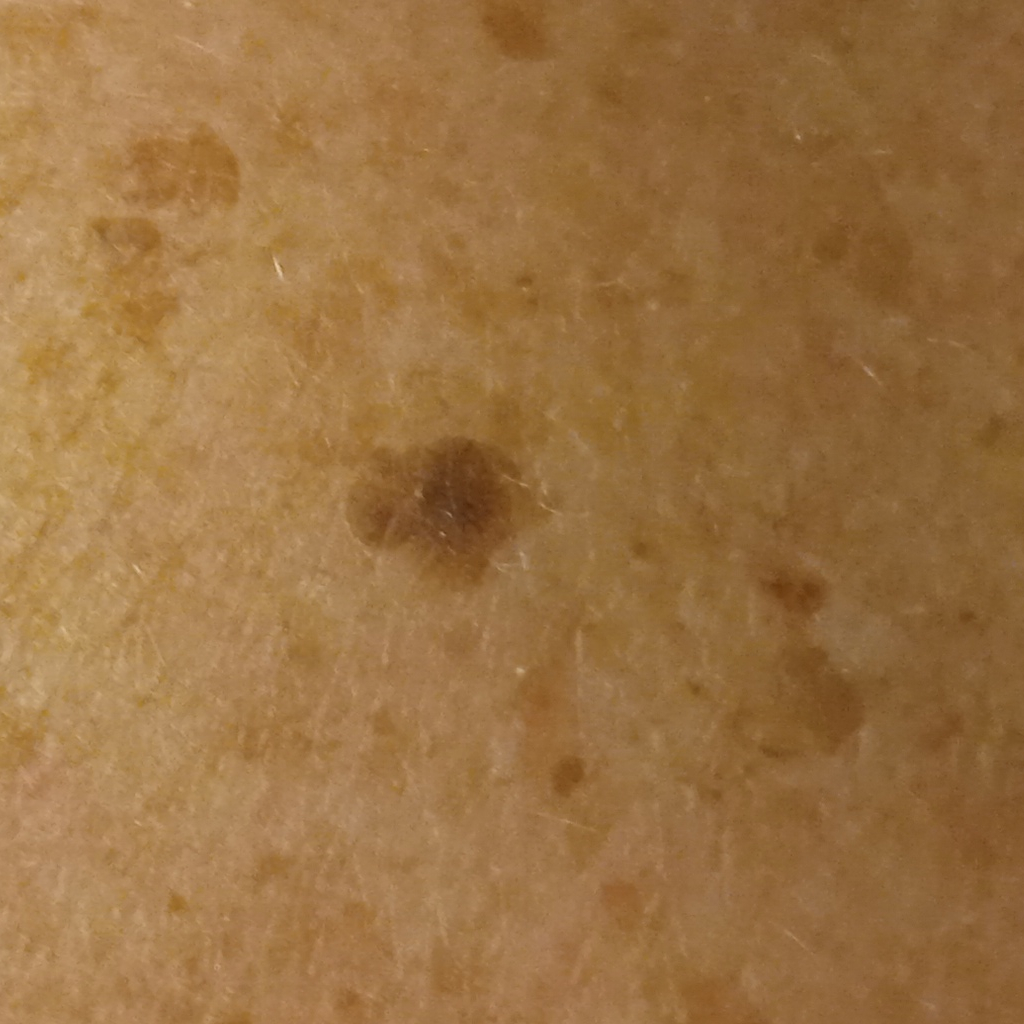The patient describes having numerous moles. A clinical close-up of a skin lesion. Collected as part of a research study, without a referral diagnosis. A female subject 78 years of age. The patient says their skin tans without first burning. Located on the back. The lesion measures approximately 5.6 mm. Dermatologist review favored a seborrheic keratosis.